A female patient roughly 55 years of age. Contact-polarized dermoscopy of a skin lesion. The patient was assessed as skin type II — 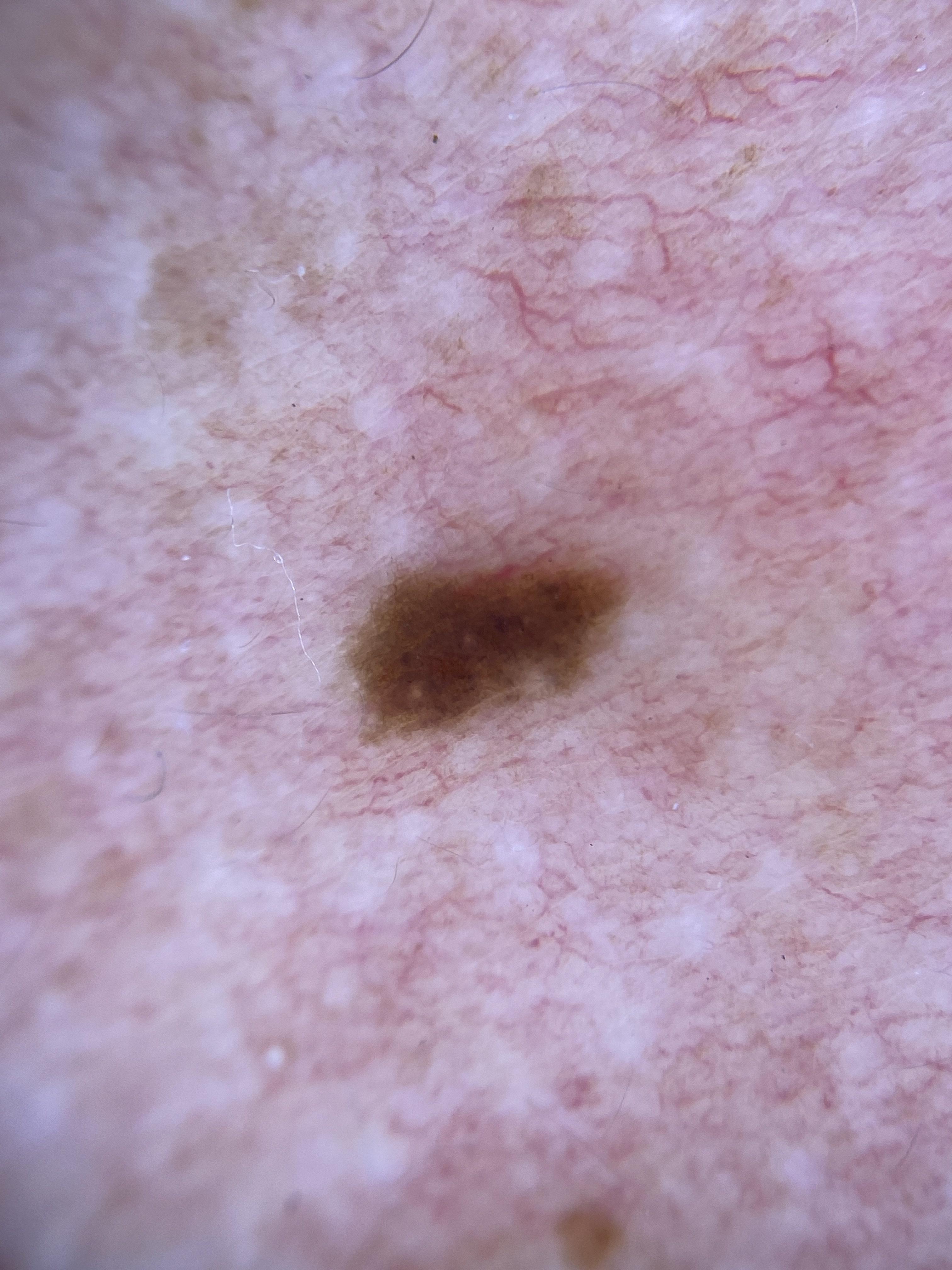The lesion involves the trunk.
The clinical impression was a nevus.